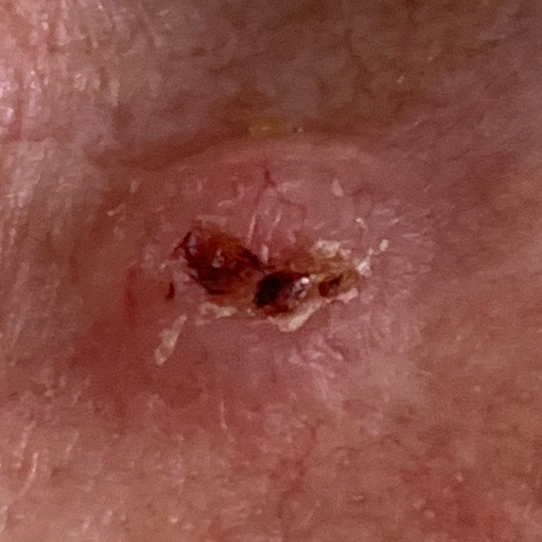{"skin_type": "III", "image": "clinical photo", "patient": {"age": 66, "gender": "female"}, "risk_factors": {"positive": ["prior skin cancer (patient or family)", "prior cancer (patient or family)"], "negative": ["smoking"]}, "lesion_location": "the nose", "lesion_size": {"diameter_1_mm": 4.0, "diameter_2_mm": 3.0}, "symptoms": {"present": ["bleeding", "elevation", "itching"], "absent": ["pain"]}, "diagnosis": {"name": "basal cell carcinoma", "code": "BCC", "malignancy": "malignant", "confirmation": "histopathology"}}